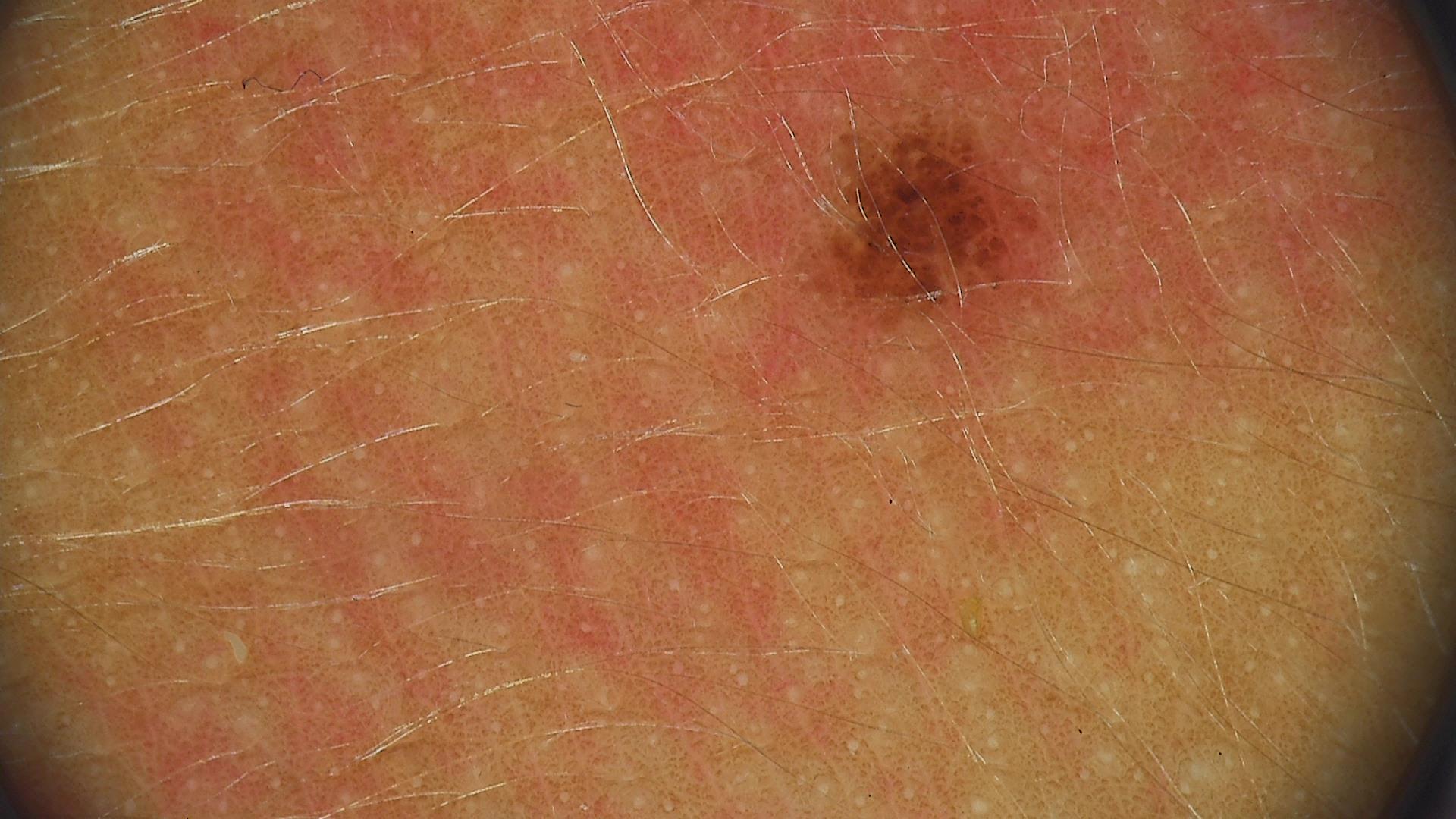Dermoscopy of a skin lesion. The architecture is that of a banal lesion. The diagnostic label was a compound nevus.